Skin tone: Fitzpatrick skin type VI. Close-up view: 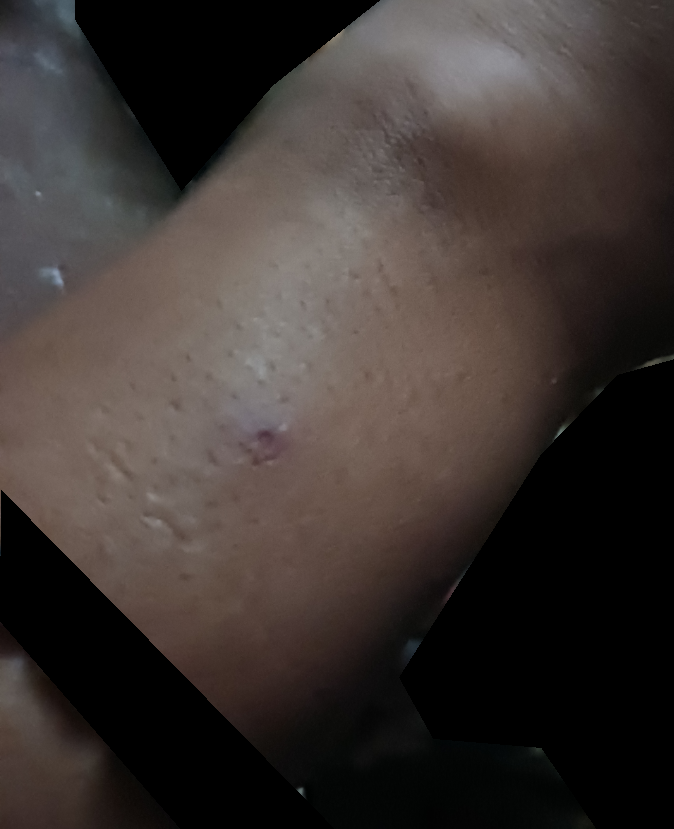assessment: unable to determine.